Dermoscopy of a skin lesion, a male patient approximately 75 years of age: 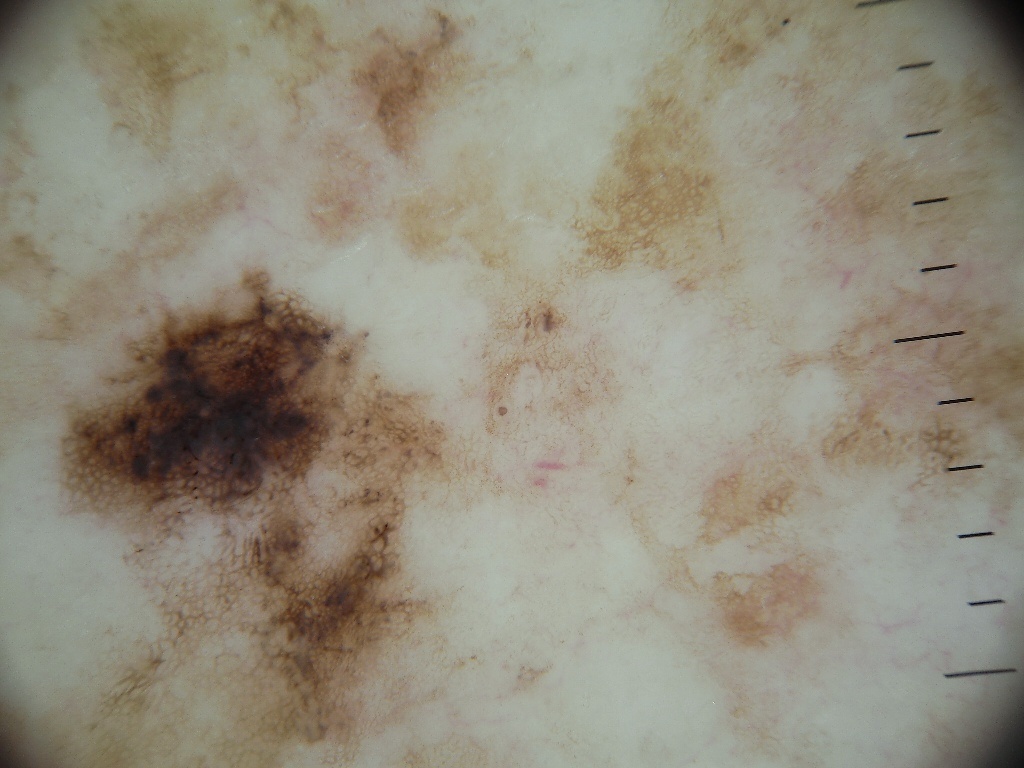In (x1, y1, x2, y2) order, the lesion's extent is bbox(41, 258, 479, 766). A moderately sized lesion. On dermoscopy, the lesion shows pigment network. Confirmed on histopathology as a melanoma.